Located on the back of the torso, front of the torso and head or neck. This is a close-up image: 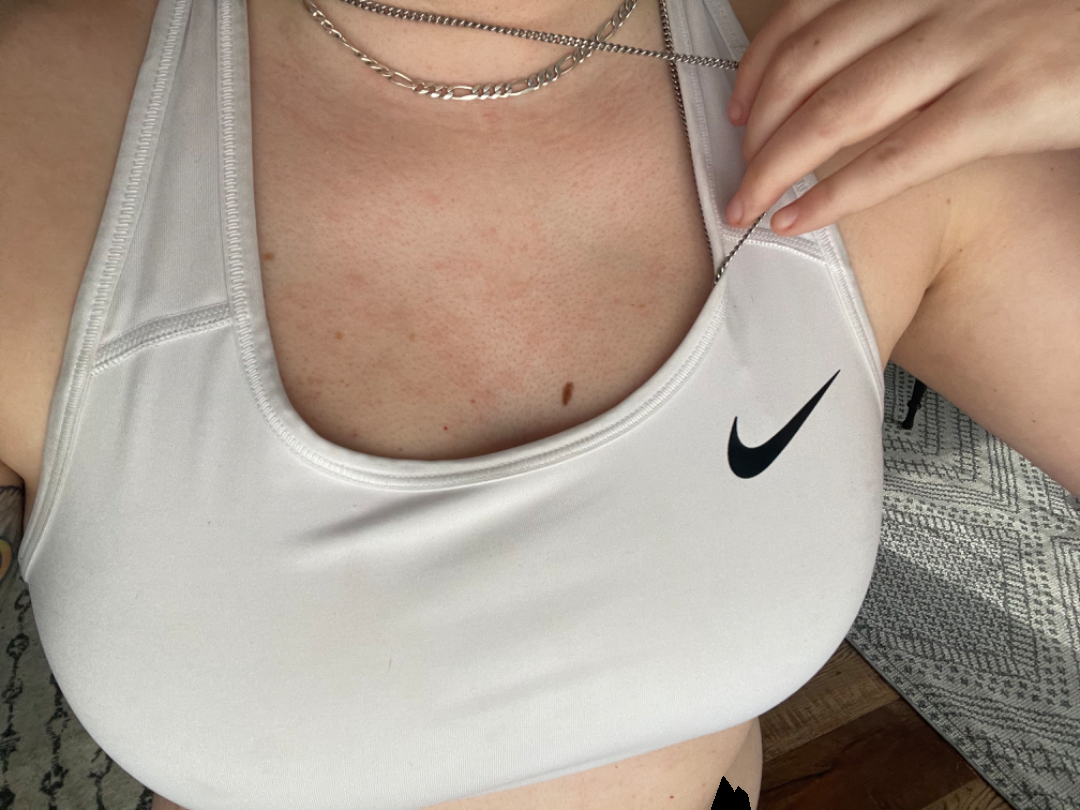Assessment:
The condition could not be reliably identified from the image.
Clinical context:
The patient reports associated mouth sores. The patient reports the lesion is raised or bumpy. Present for about one day.